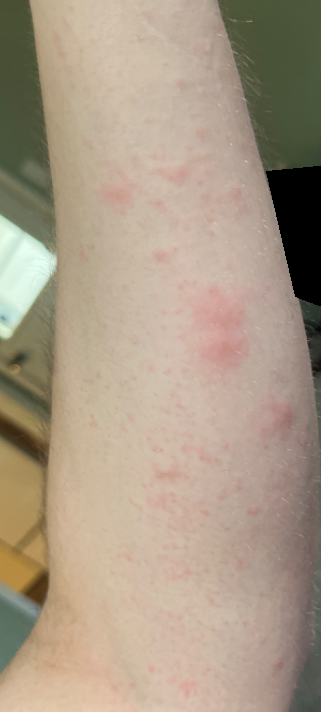{"shot_type": "close-up", "body_site": "arm", "symptoms": "itching", "differential": "Urticaria"}